A male patient aged around 25, dermoscopy of a skin lesion.
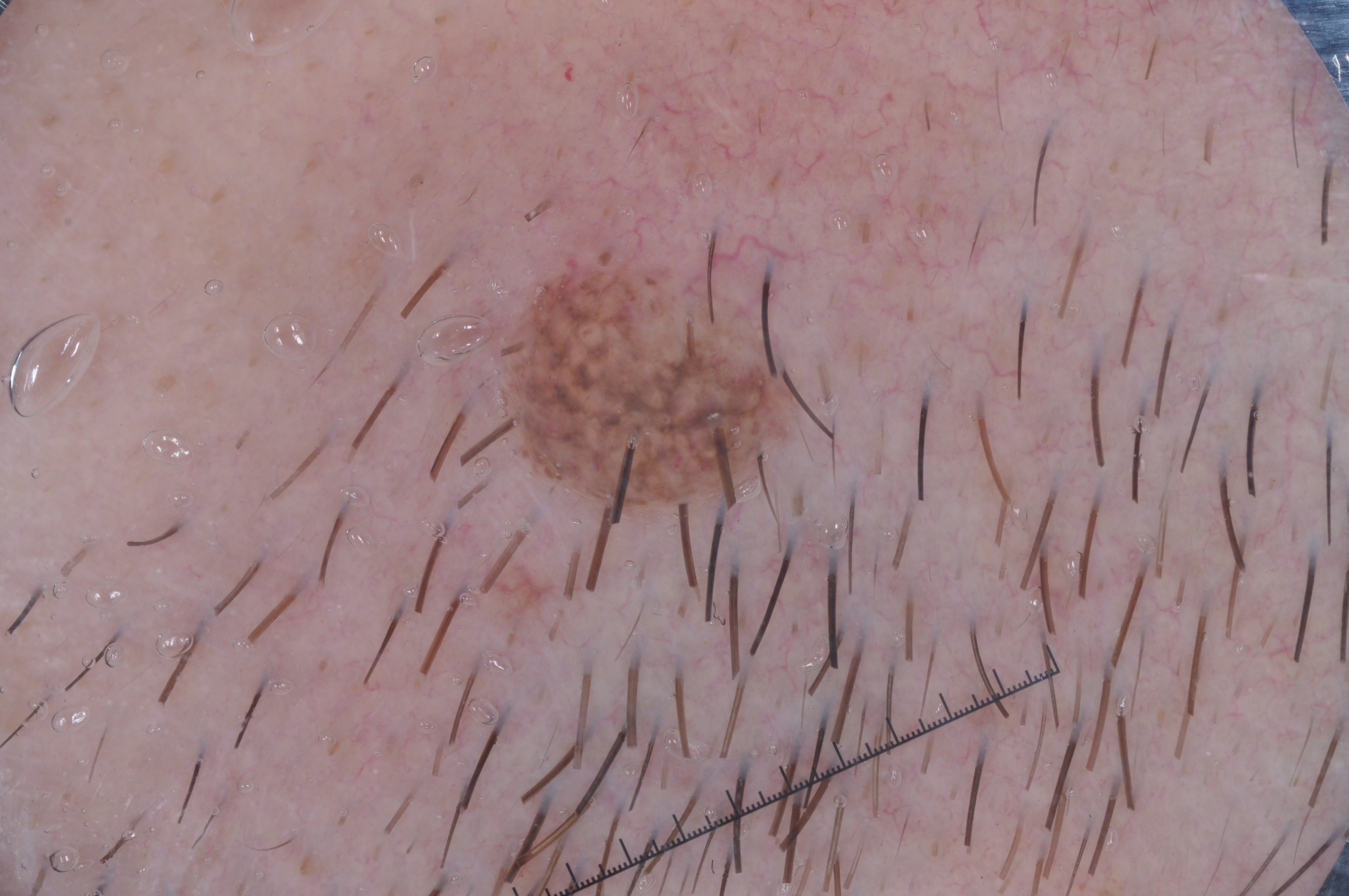In (x1, y1, x2, y2) order, the visible lesion spans bbox=[474, 245, 801, 511].
Dermoscopic examination shows no pigment network, milia-like cysts, negative network, or streaks.
Consistent with a melanocytic nevus.